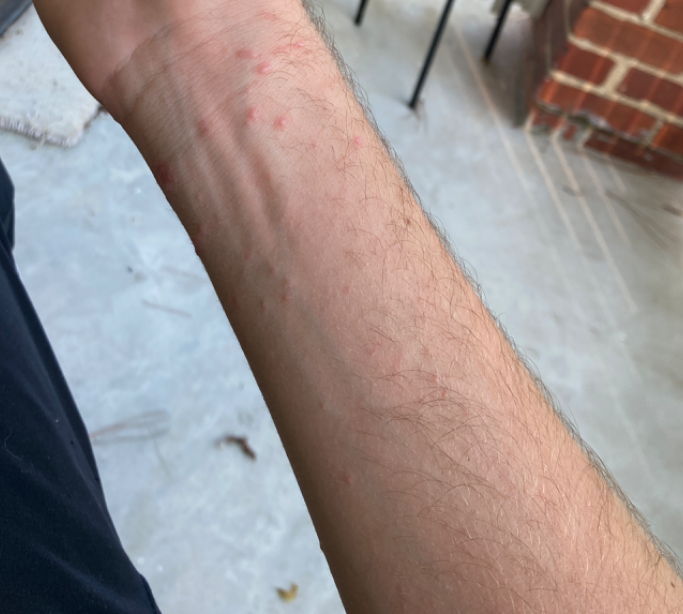lesion symptoms: itching, bothersome appearance and pain | contributor: male, age 18–29 | shot type: at a distance | body site: leg, back of the hand, front of the torso, arm and top or side of the foot | history: one to four weeks | lesion texture: raised or bumpy | differential diagnosis: Scabies, Insect Bite and Allergic Contact Dermatitis were each considered, in no particular order.